Located on the leg and top or side of the foot · this image was taken at an angle — 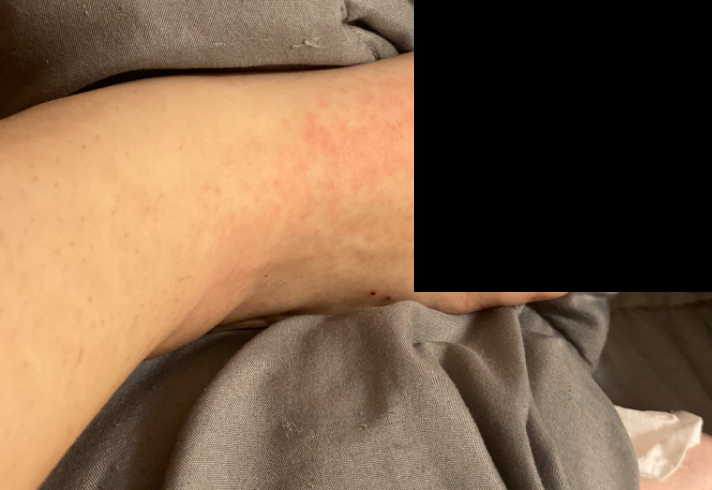| feature | finding |
|---|---|
| assessment | unable to determine |